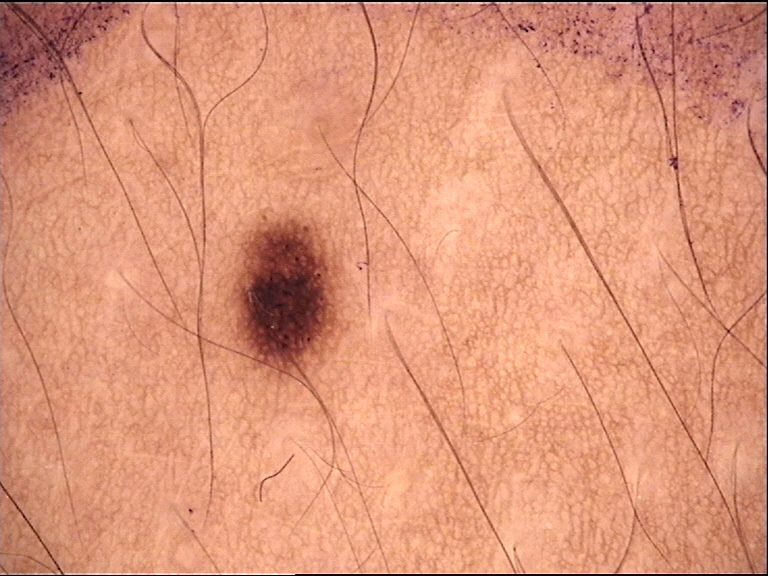Case: A dermoscopy image of a single skin lesion. This is a banal lesion. Conclusion: The diagnosis was a junctional nevus.